Located on the front of the torso · an image taken at an angle — 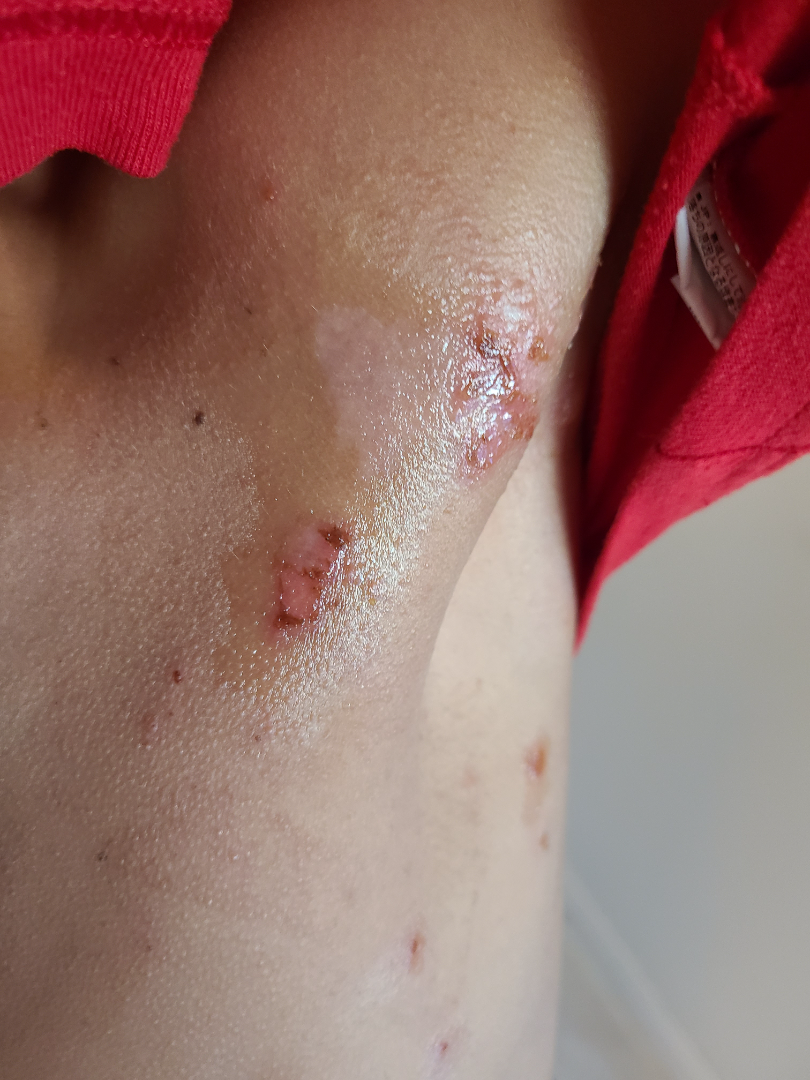Findings:
– impression · the differential includes Impetigo, Pemphigus vulgaris and Linear IgA disease, with no clear leading consideration